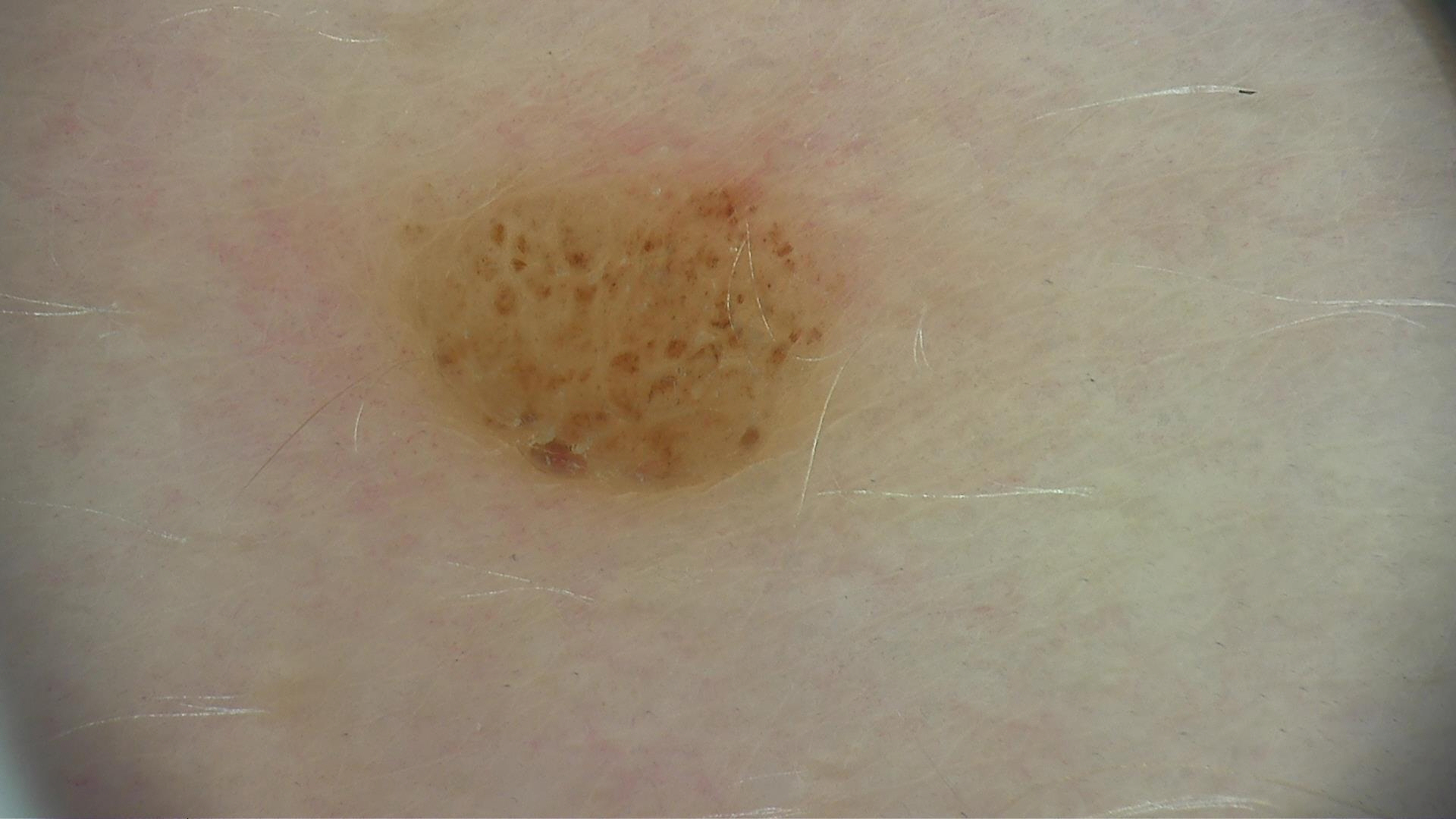* modality — dermoscopy
* category — banal
* label — compound nevus (expert consensus)